Female contributor, age 40–49; the affected area is the arm; an image taken at a distance: 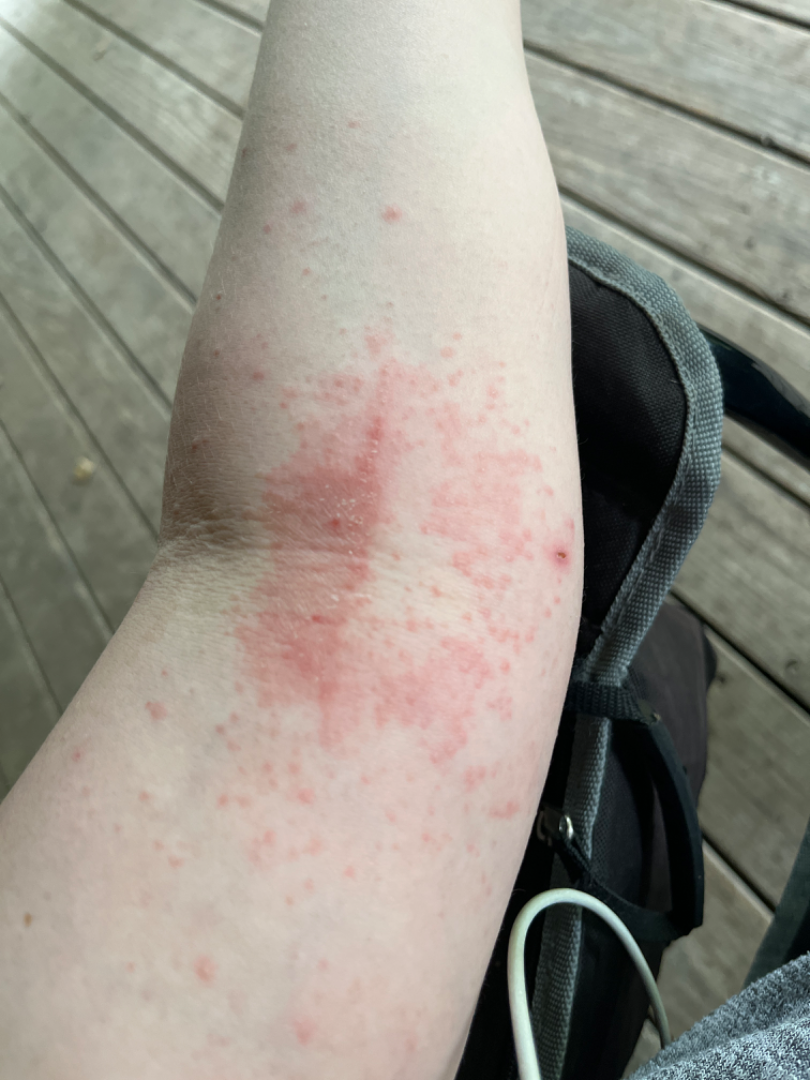lesion symptoms — itching | history — one to four weeks | patient describes the issue as — a rash | differential diagnosis — three dermatologists independently reviewed the case: most consistent with Eczema; possibly Allergic Contact Dermatitis; a more distant consideration is Drug Rash.